Dermoscopy of a skin lesion.
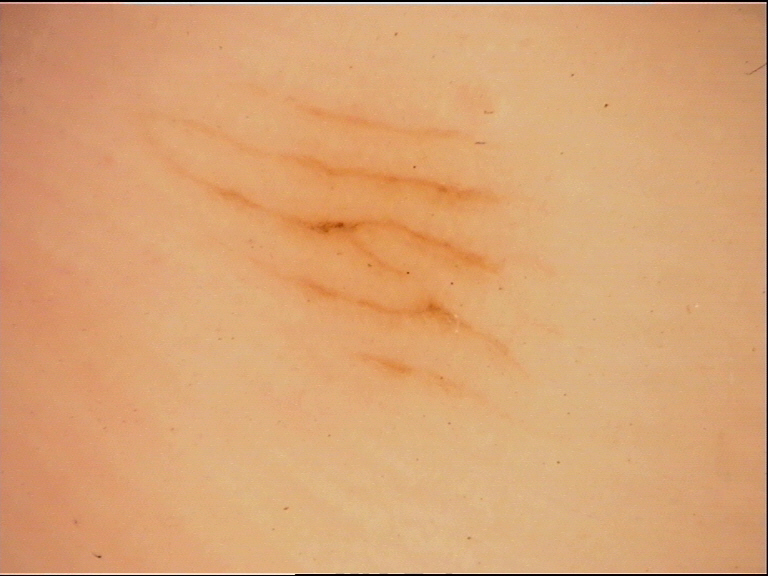category = banal; diagnosis = acral junctional nevus (expert consensus).